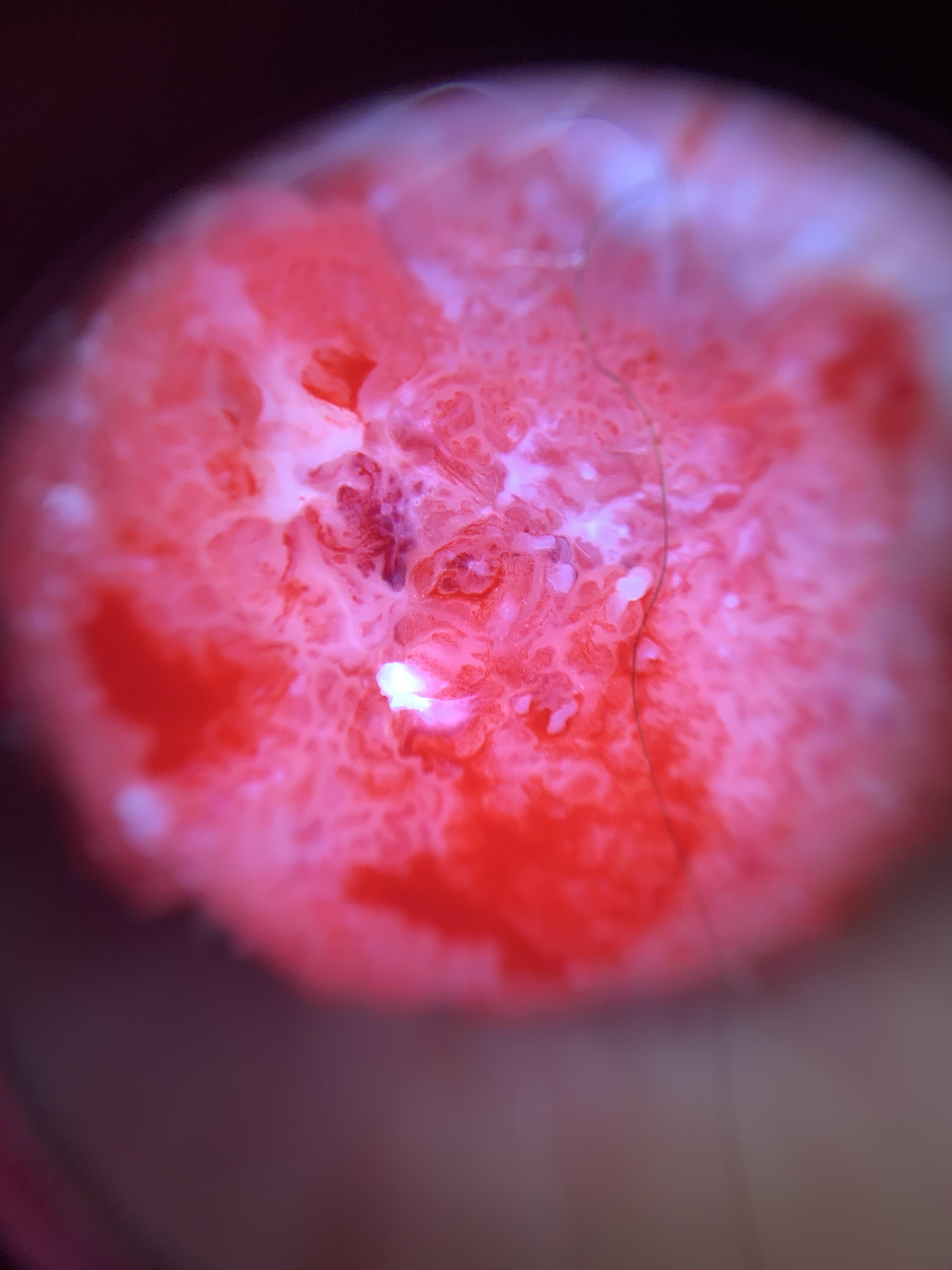A male subject in their mid-80s or older. The patient was assessed as skin type II. A dermoscopic image of a skin lesion. Confirmed on histopathology as a lesion of epidermal origin — a squamous cell carcinoma.